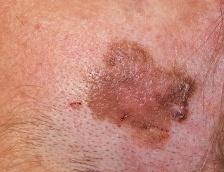Biopsy-confirmed as a melanoma.